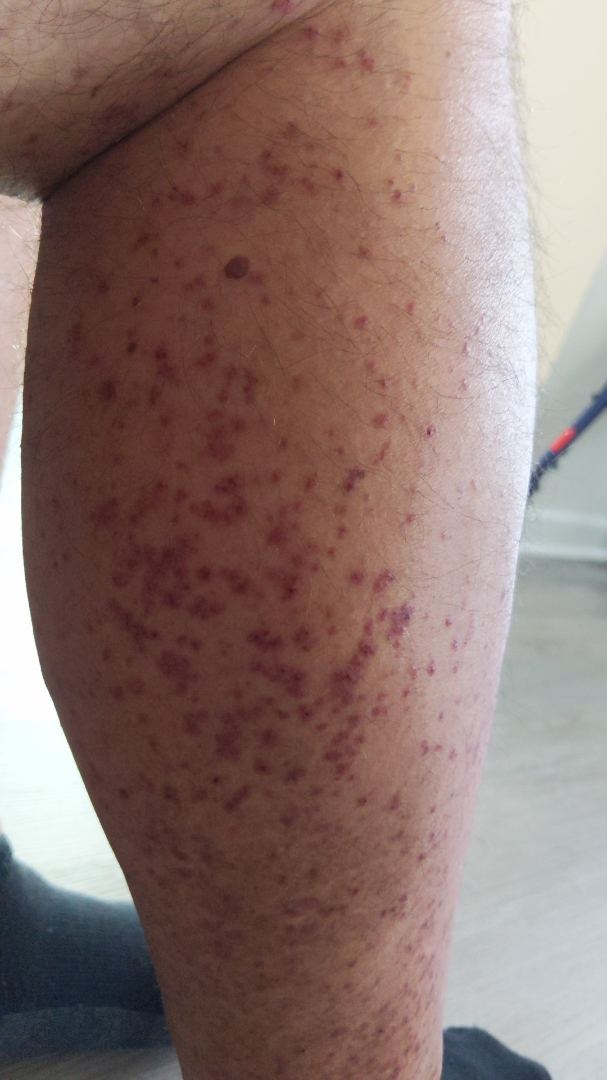Notes:
* impression: consistent with Leukocytoclastic Vasculitis